A male subject, aged approximately 45 · a dermoscopic image of a skin lesion:
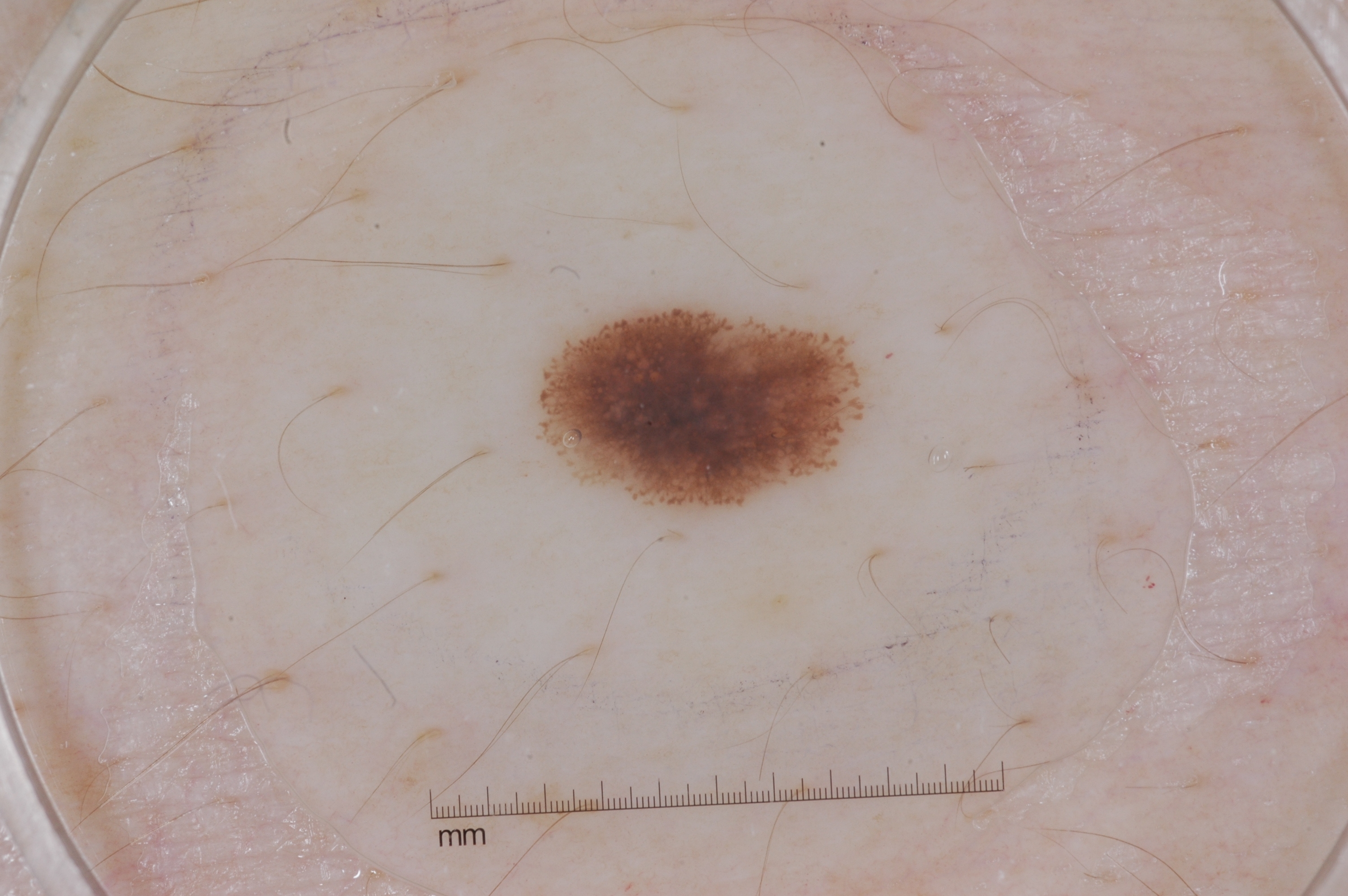dermoscopic features = pigment network and streaks
lesion extent = ~5% of the field
lesion location = [529,295,875,522]
diagnosis = a melanocytic nevus